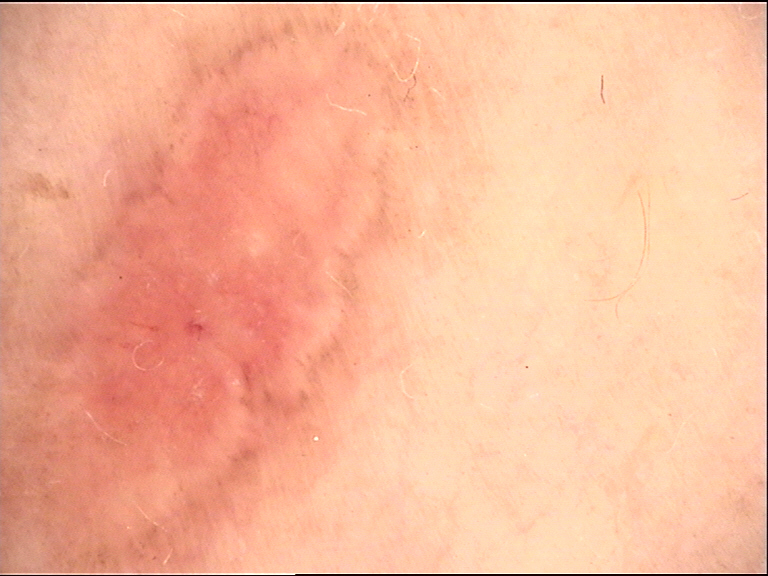Q: What did the workup show?
A: basal cell carcinoma (biopsy-proven)